The arm and back of the hand are involved; reported lesion symptoms include bothersome appearance and itching; the patient indicates associated fatigue and chills; the photograph was taken at a distance; the lesion is described as rough or flaky and raised or bumpy — 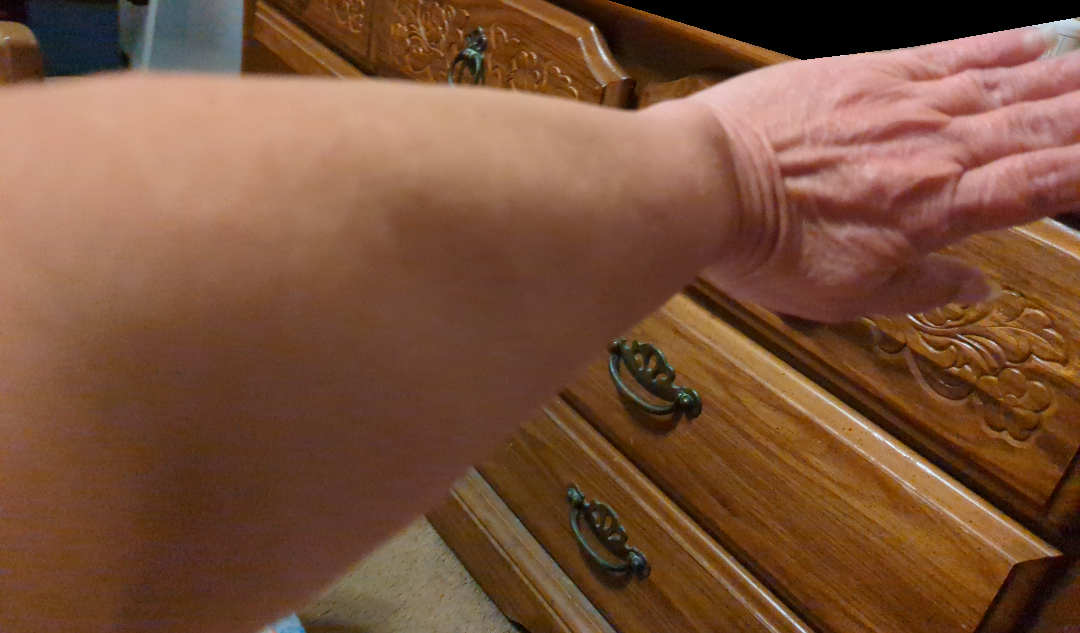<summary>
<differential>
  <leading>Folliculitis</leading>
  <considered>Eczema</considered>
</differential>
</summary>